A clinical photograph showing a skin lesion. A female subject 71 years of age. Referred with a clinical suspicion of basal cell carcinoma — 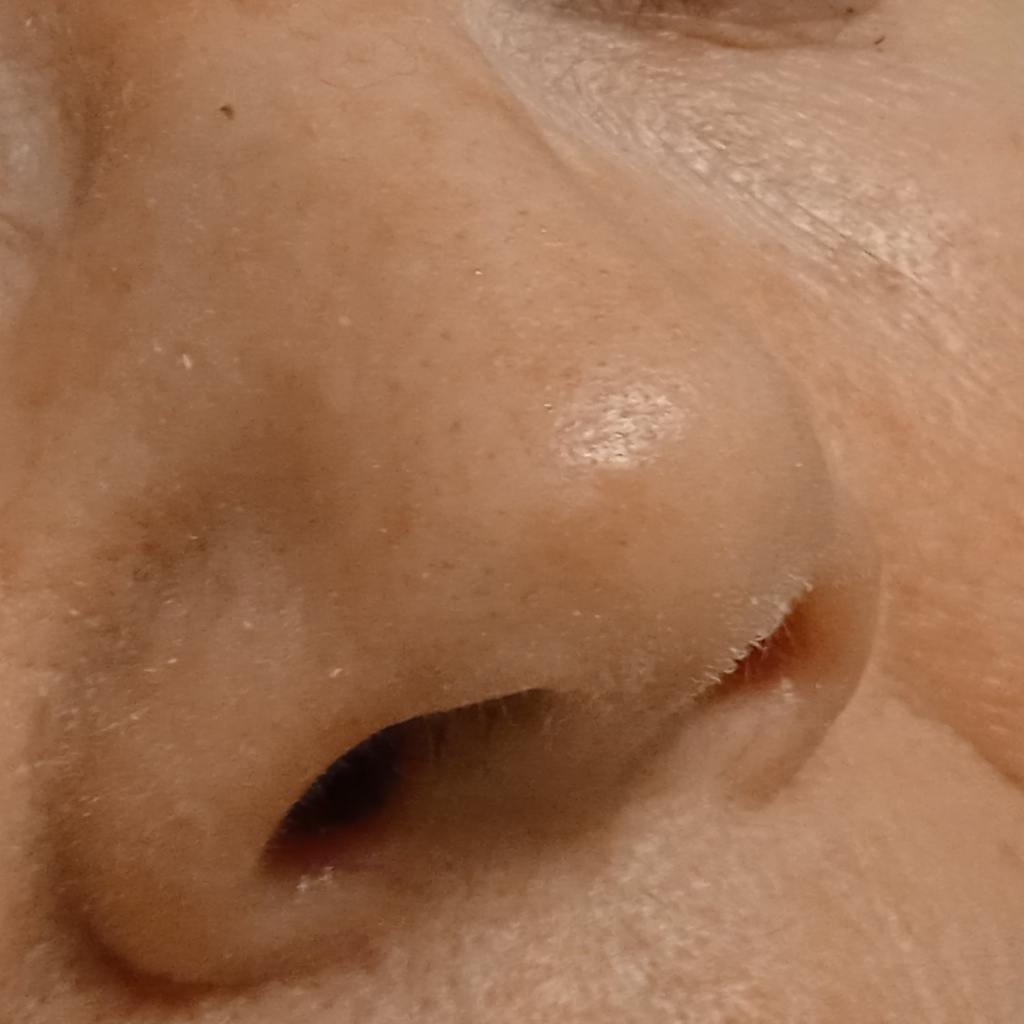The lesion is located on the face. Measuring roughly 7.3 mm. Dermatologist review favored an actinic keratosis.